The patient reports a personal history of cancer · the patient says their skin reddens with sun exposure · a male subject 78 years old · few moles overall by the patient's own estimate · dermoscopy of a skin lesion.
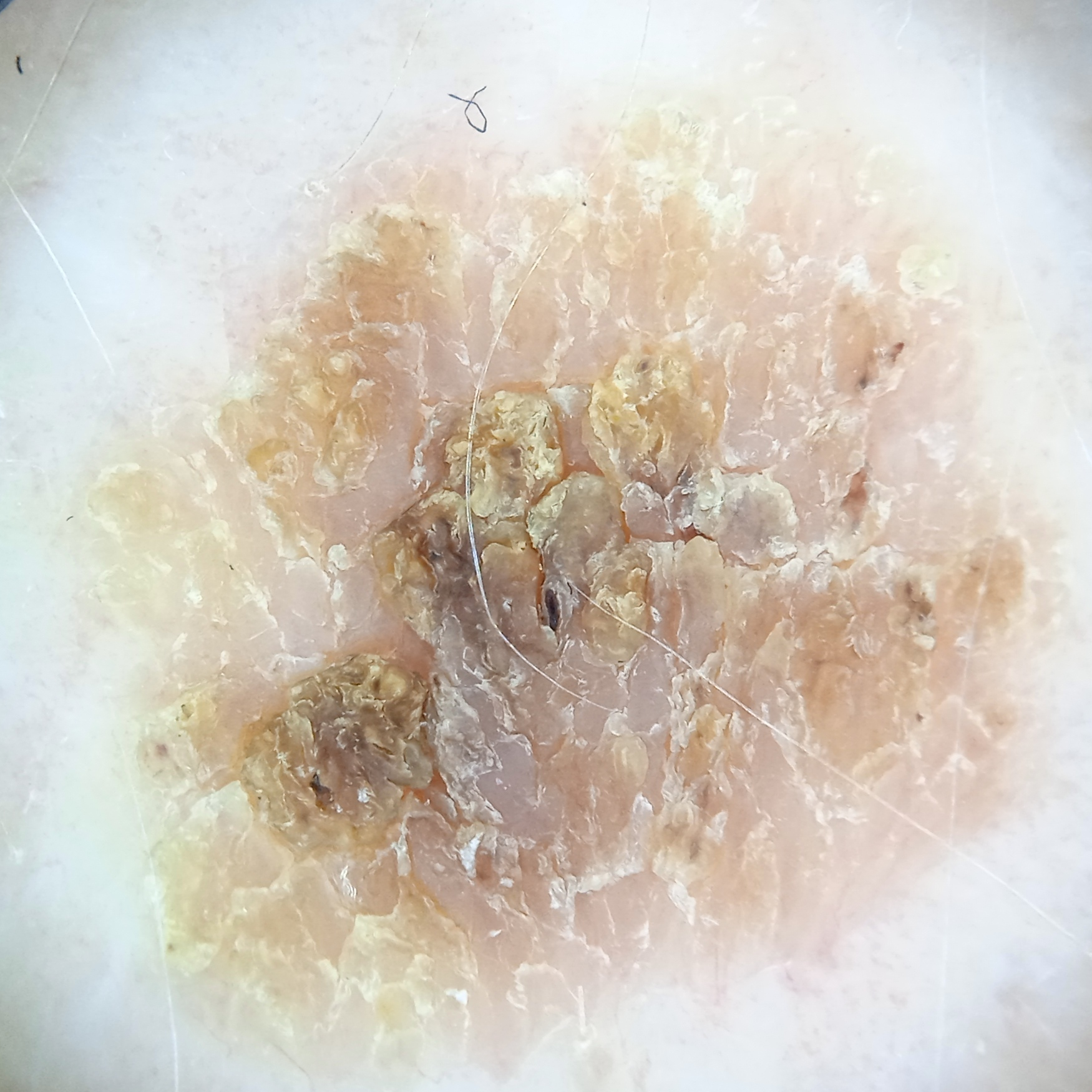- anatomic site — the back
- diagnostic label — seborrheic keratosis (dermatologist consensus)